A female subject aged 53-57. Fitzpatrick II. A contact-polarized dermoscopy image of a skin lesion — 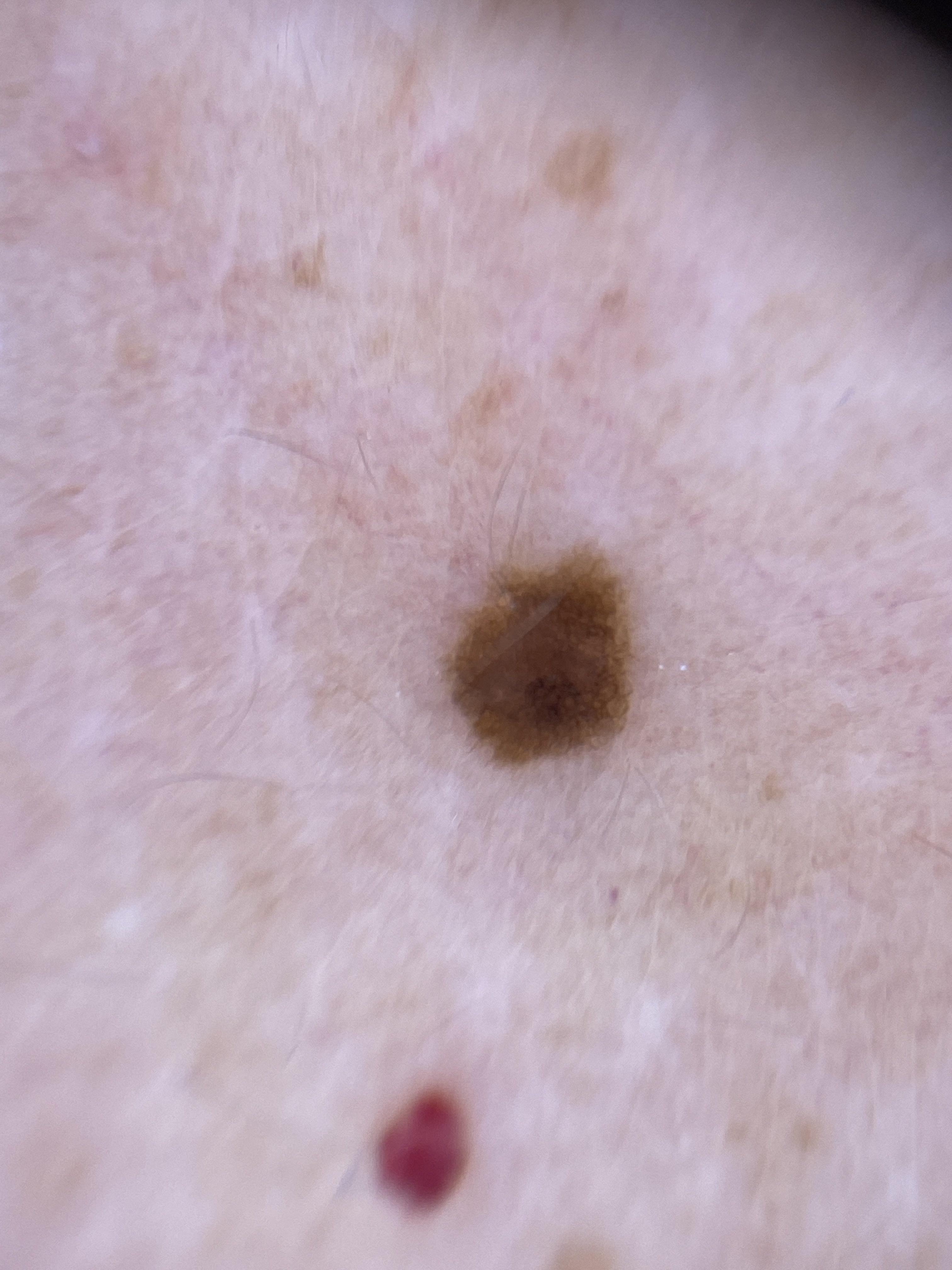site: the trunk; assessment: Nevus.